The photograph is a close-up of the affected area. Texture is reported as flat — 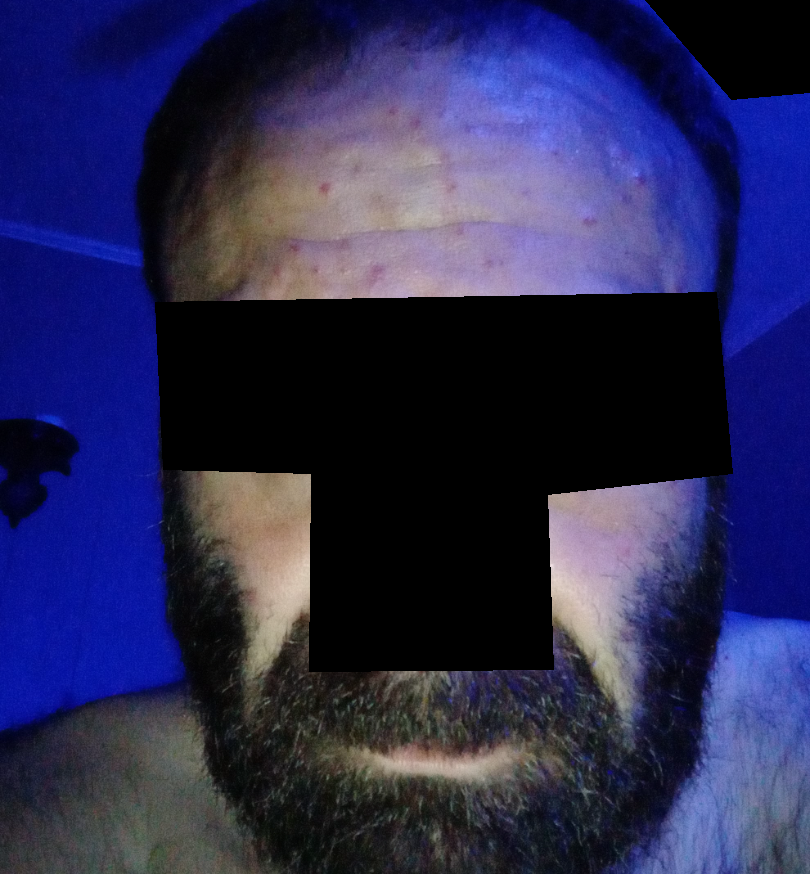Q: Could the case be diagnosed?
A: unable to determine